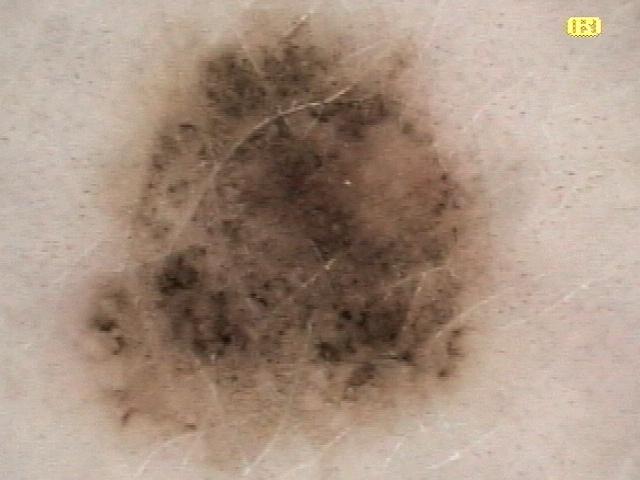Notes:
• diagnostic label · Nevus (biopsy-proven)